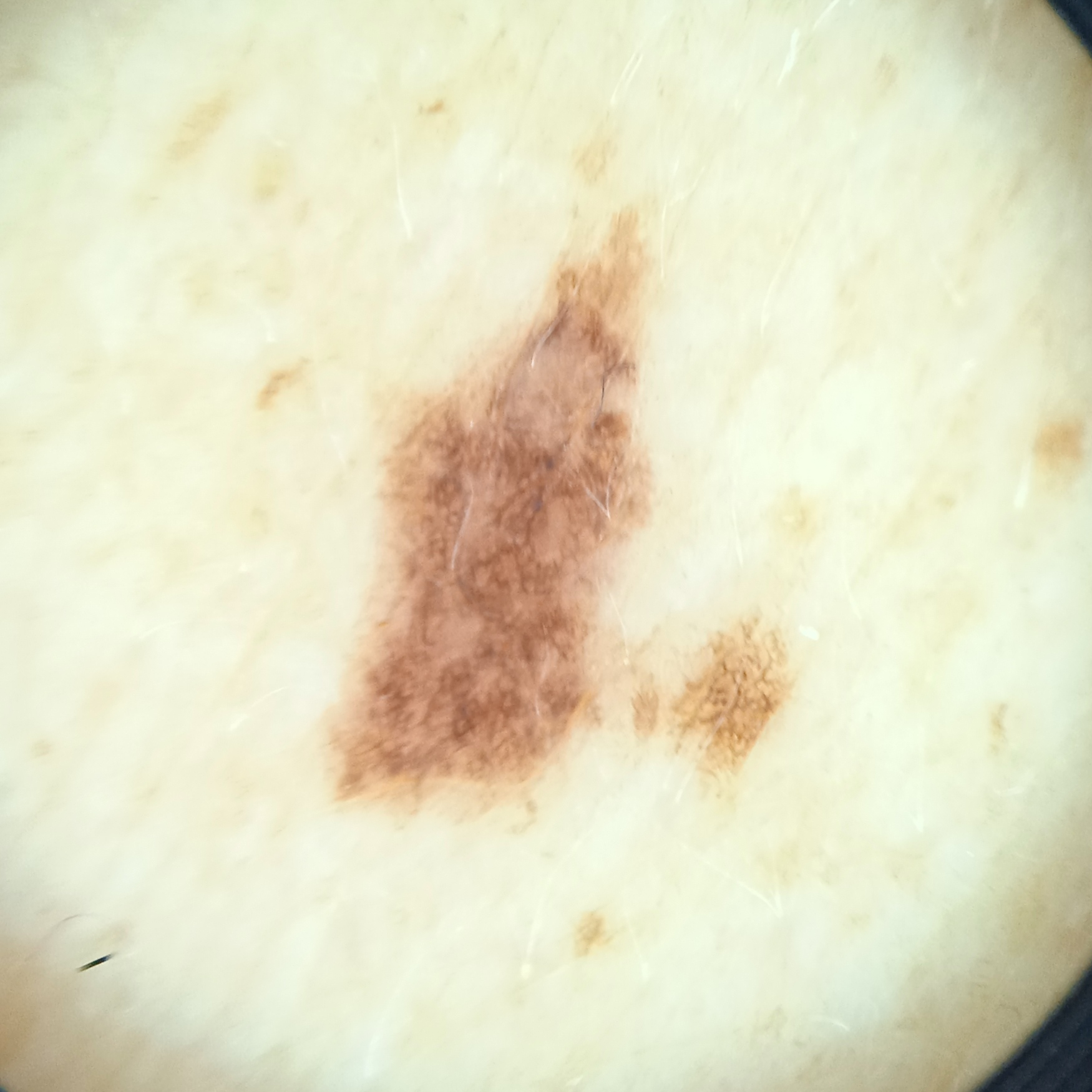| feature | finding |
|---|---|
| referral context | clinical suspicion of melanocytic nevus |
| modality | dermoscopy |
| subject | female, 64 years old |
| size | 8.3 mm |
| diagnosis | atypical (dysplastic) nevus — biopsy-proven |